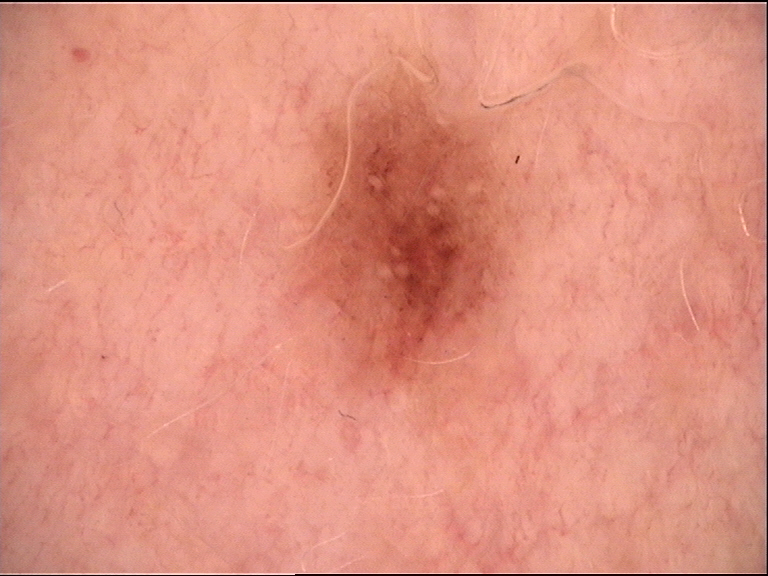Diagnosed as a benign lesion — a dysplastic junctional nevus.